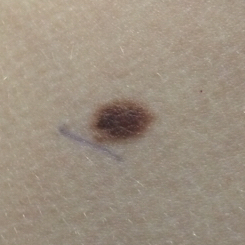patient:
  age: 27
  gender: female
image: clinical photo
risk_factors:
  positive:
    - prior cancer (patient or family)
    - alcohol use
  negative:
    - smoking
skin_type: IV
lesion_location: the abdomen
lesion_size:
  diameter_1_mm: 8.0
  diameter_2_mm: 5.0
symptoms:
  present:
    - growth
    - elevation
diagnosis:
  name: nevus
  code: NEV
  malignancy: benign
  confirmation: histopathology